The chart documents a first-degree relative with melanoma. A female patient approximately 35 years of age — 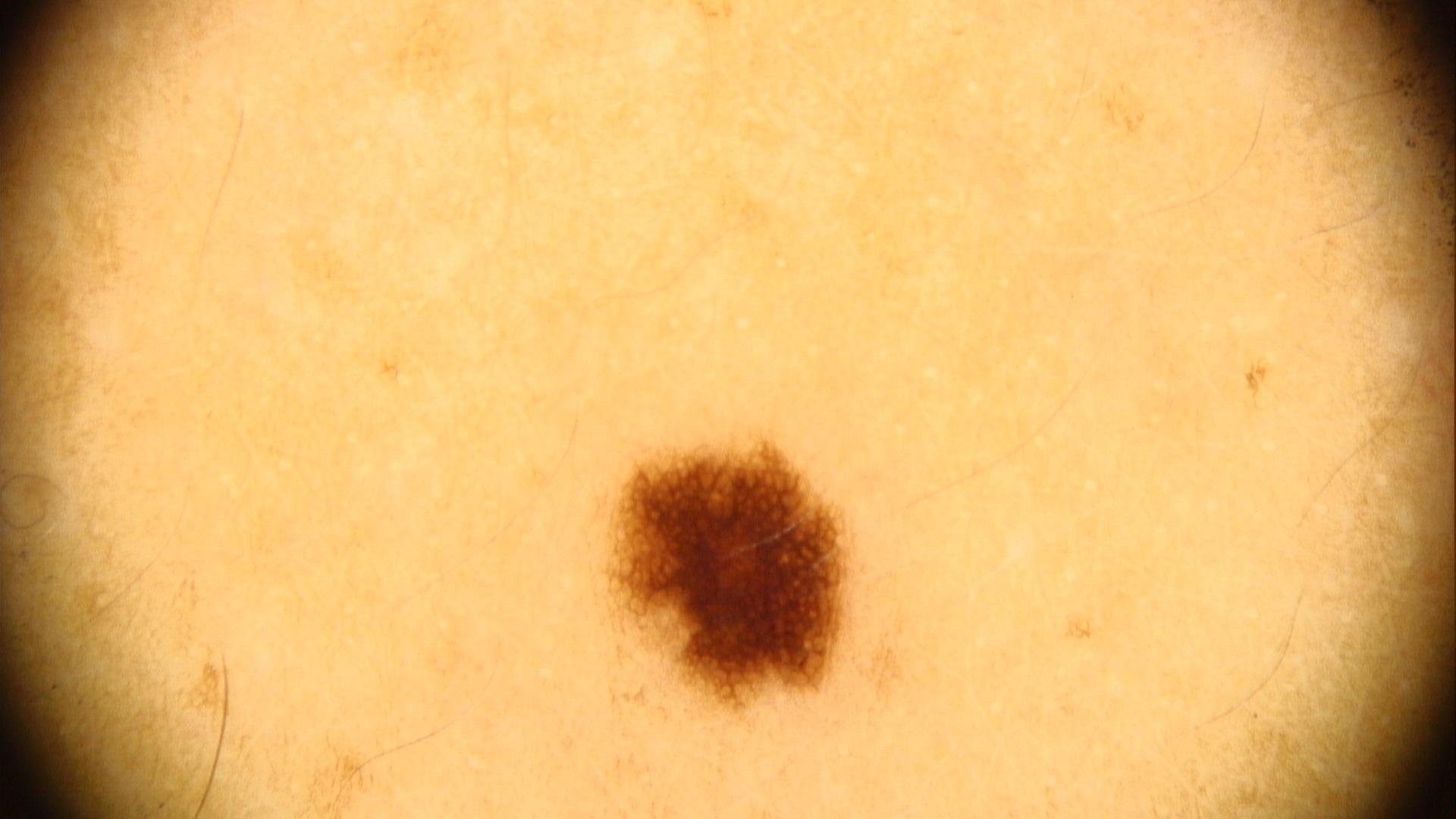Q: Where on the body is the lesion?
A: a lower extremity
Q: What was the clinical impression?
A: Nevus